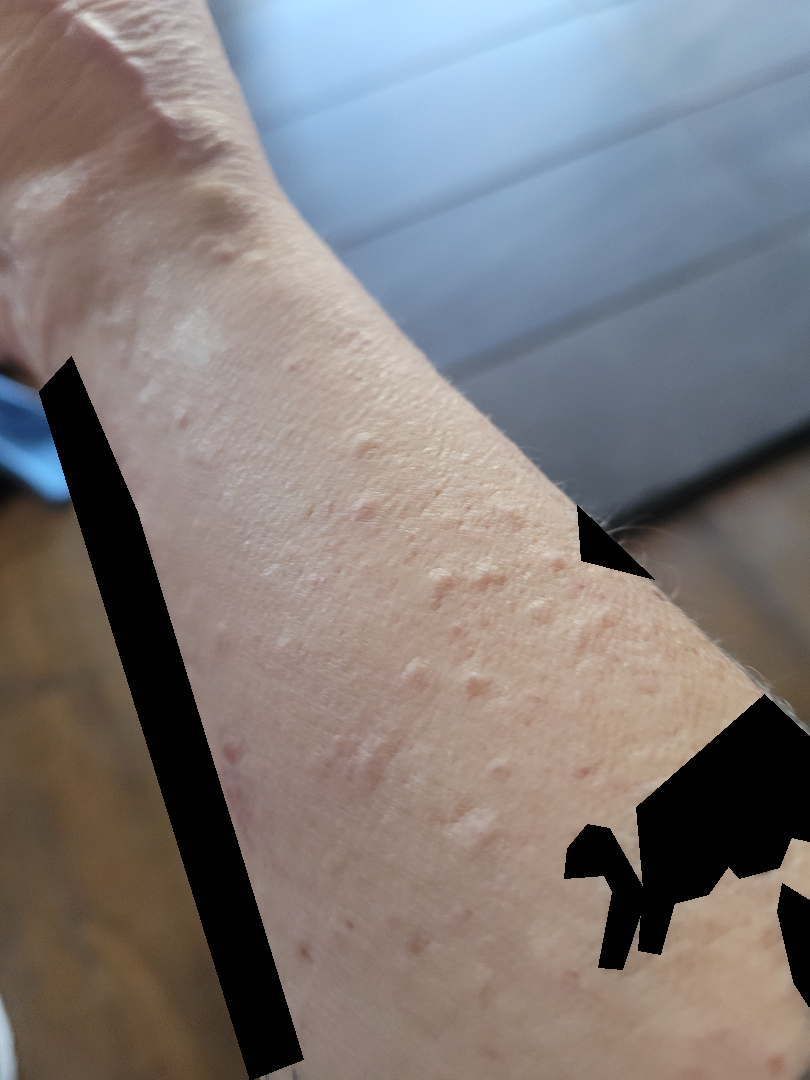<summary>
  <assessment>could not be assessed</assessment>
  <shot_type>close-up</shot_type>
  <skin_tone>
    <fitzpatrick>II</fitzpatrick>
    <monk_skin_tone>1, 2</monk_skin_tone>
  </skin_tone>
</summary>